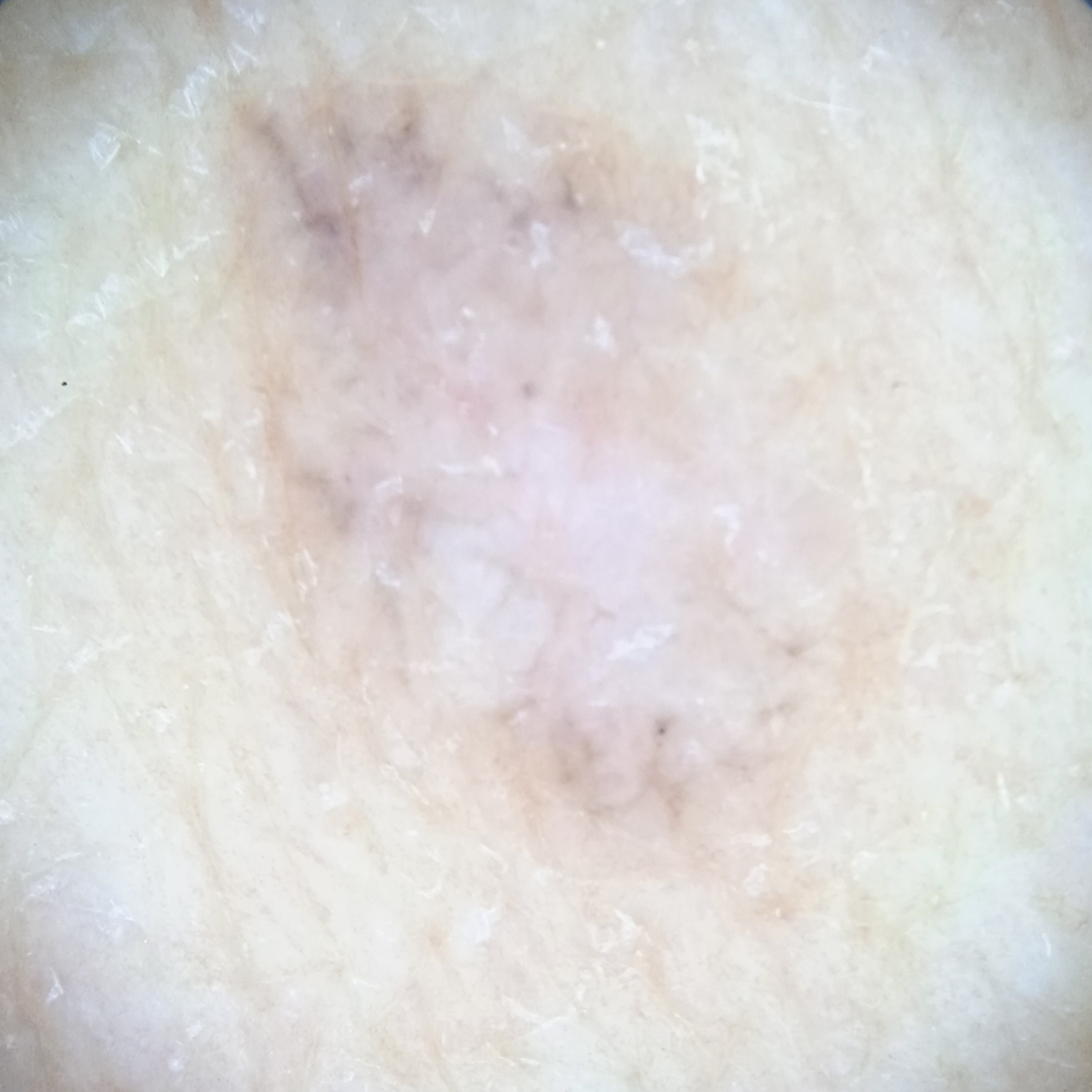Few moles overall by the patient's own estimate.
Imaged for a research study, with no referral diagnosis recorded.
By self-report, a personal history of cancer and a personal history of skin cancer.
A female subject 60 years old.
A dermatoscopic image of a skin lesion.
The lesion involves the back.
The lesion was assessed as a basal cell carcinoma.